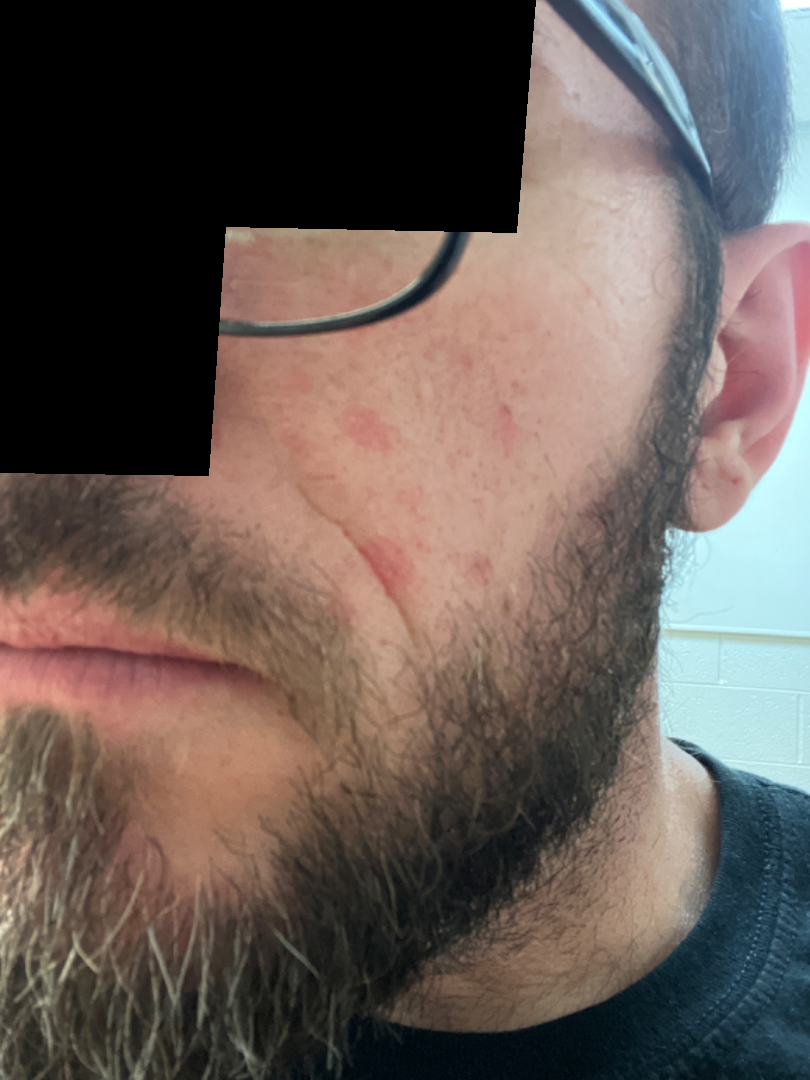This is a close-up image. The lesion involves the head or neck. Reviewed remotely by one dermatologist: most likely Rosacea; an alternative is Acne; a more distant consideration is Seborrheic Dermatitis.